A female subject aged 33 to 37 · FST III · a skin lesion imaged with contact-polarized dermoscopy · the chart records melanoma in a first-degree relative but no prior melanoma.
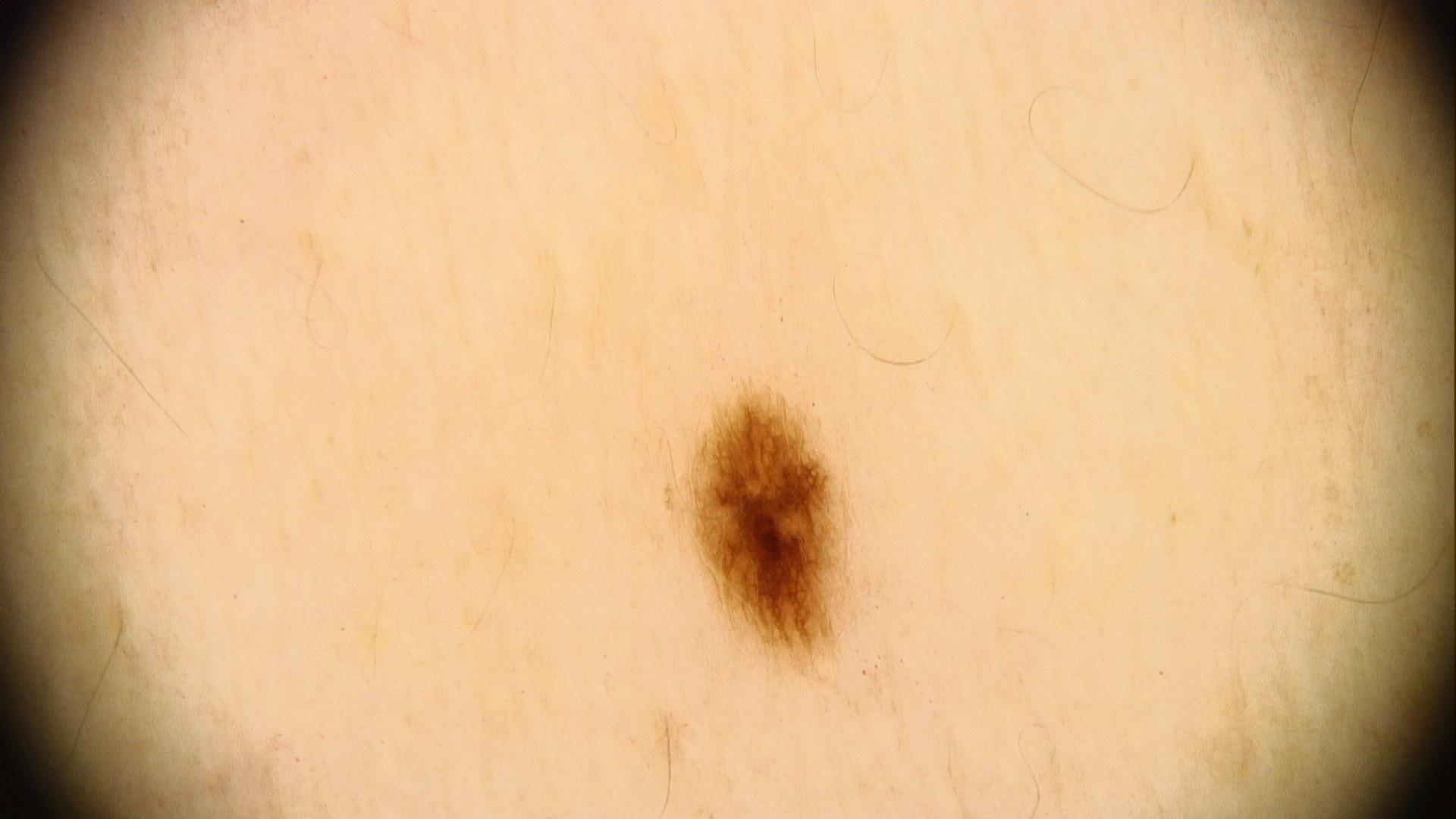Impression:
The clinical assessment was a benign lesion — a nevus.